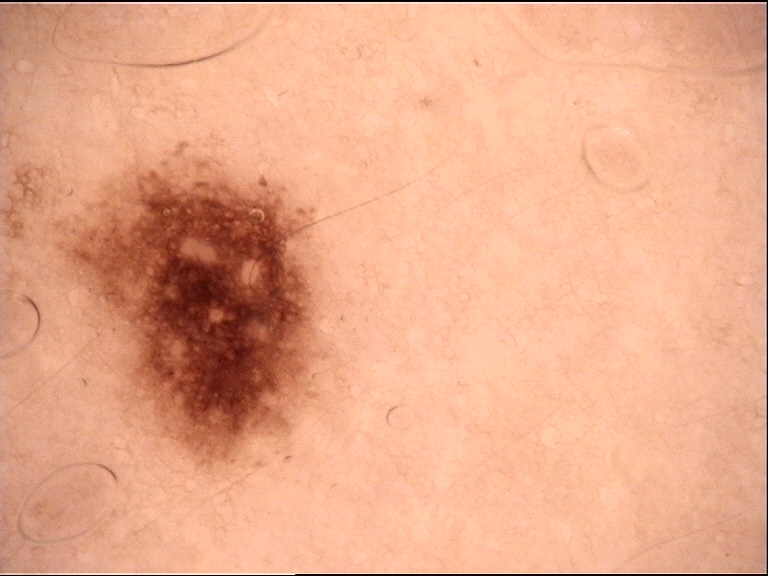diagnostic label=dysplastic junctional nevus (expert consensus).